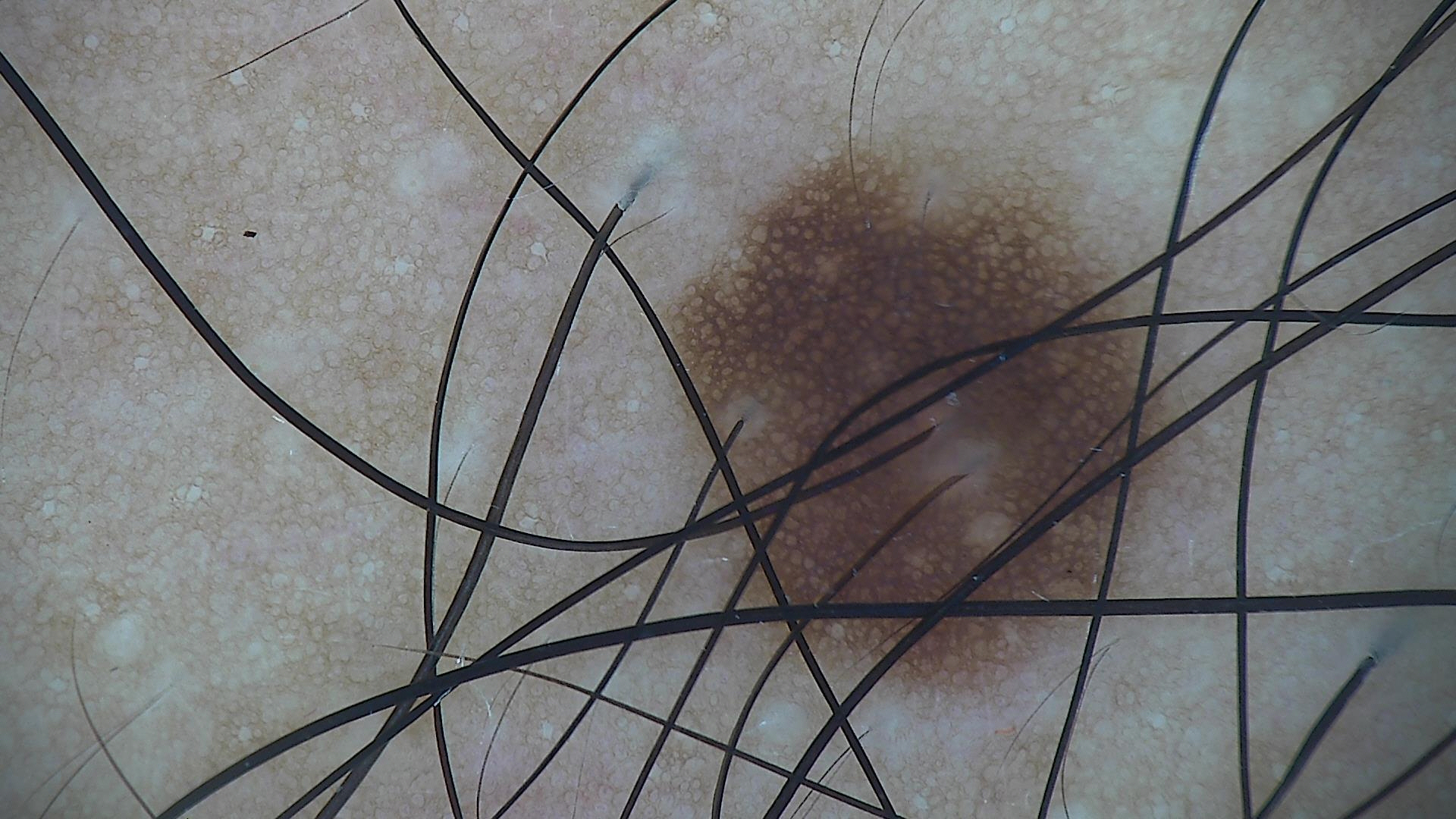Dermoscopy of a skin lesion. Diagnosed as a benign lesion — a dysplastic junctional nevus.